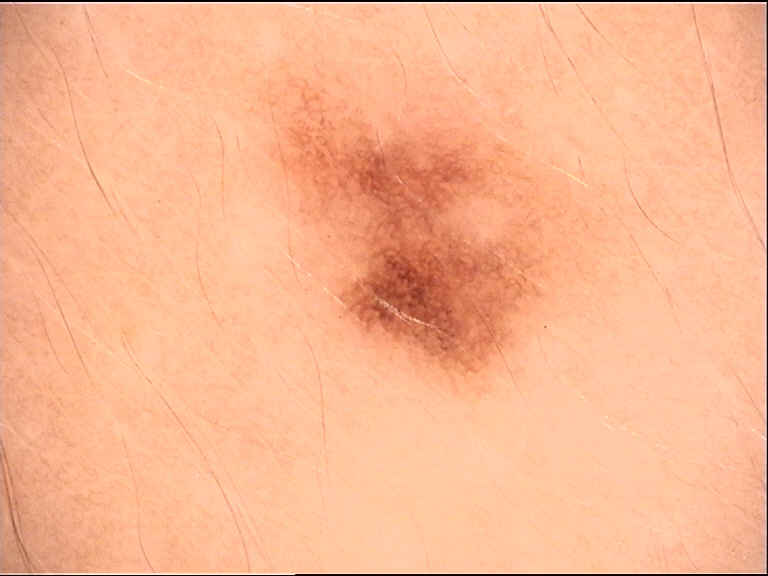Case:
A dermoscopic close-up of a skin lesion.
Conclusion:
Classified as a dysplastic junctional nevus.